A male patient 65 years of age · the patient reports a personal history of skin cancer, immunosuppression, and a family history of skin cancer · the patient describes having numerous moles · a clinical close-up of a skin lesion · the patient says their skin reddens painfully with sun exposure:
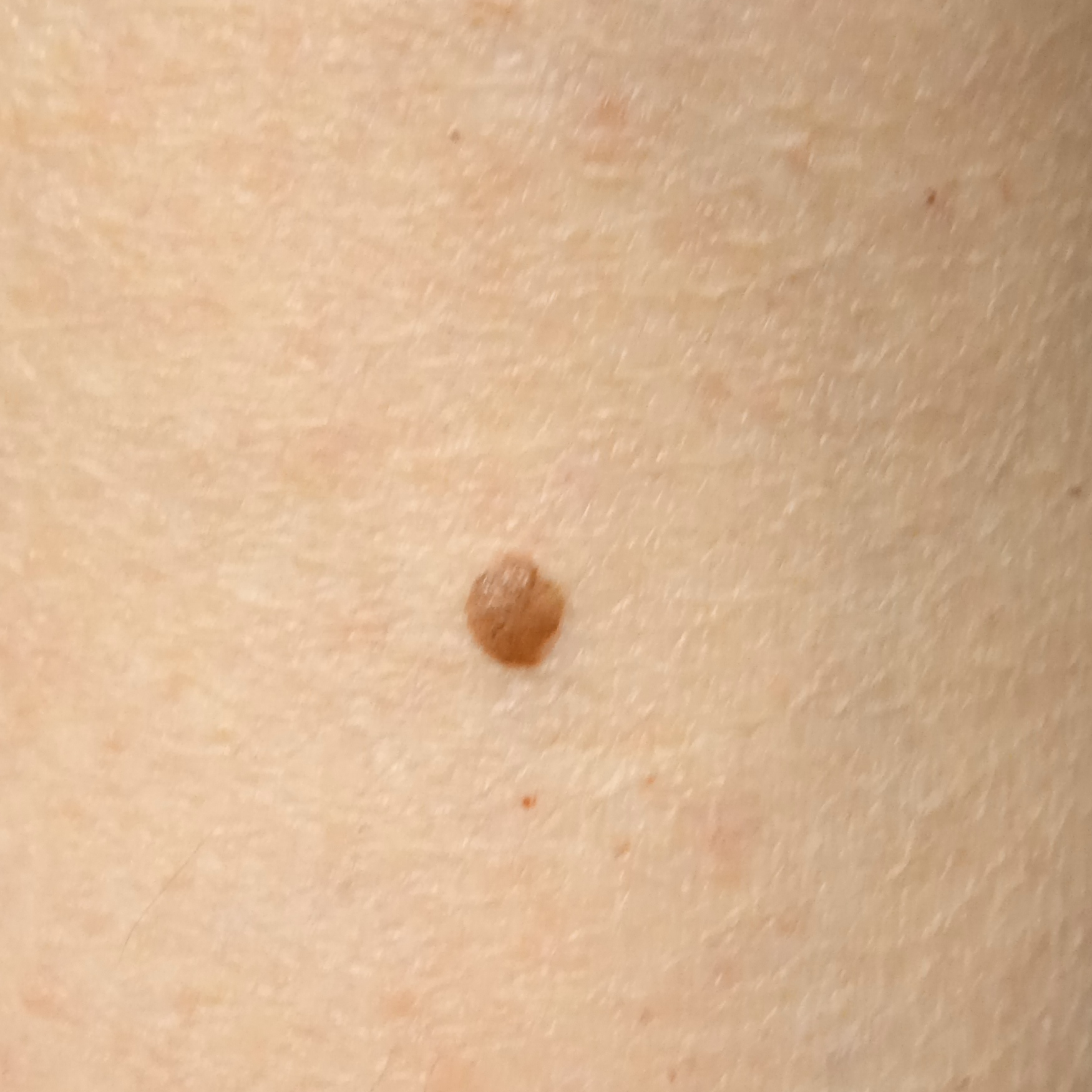The lesion is located on an arm.
The lesion is about 3 mm across.
Dermatologist review favored a melanocytic nevus.